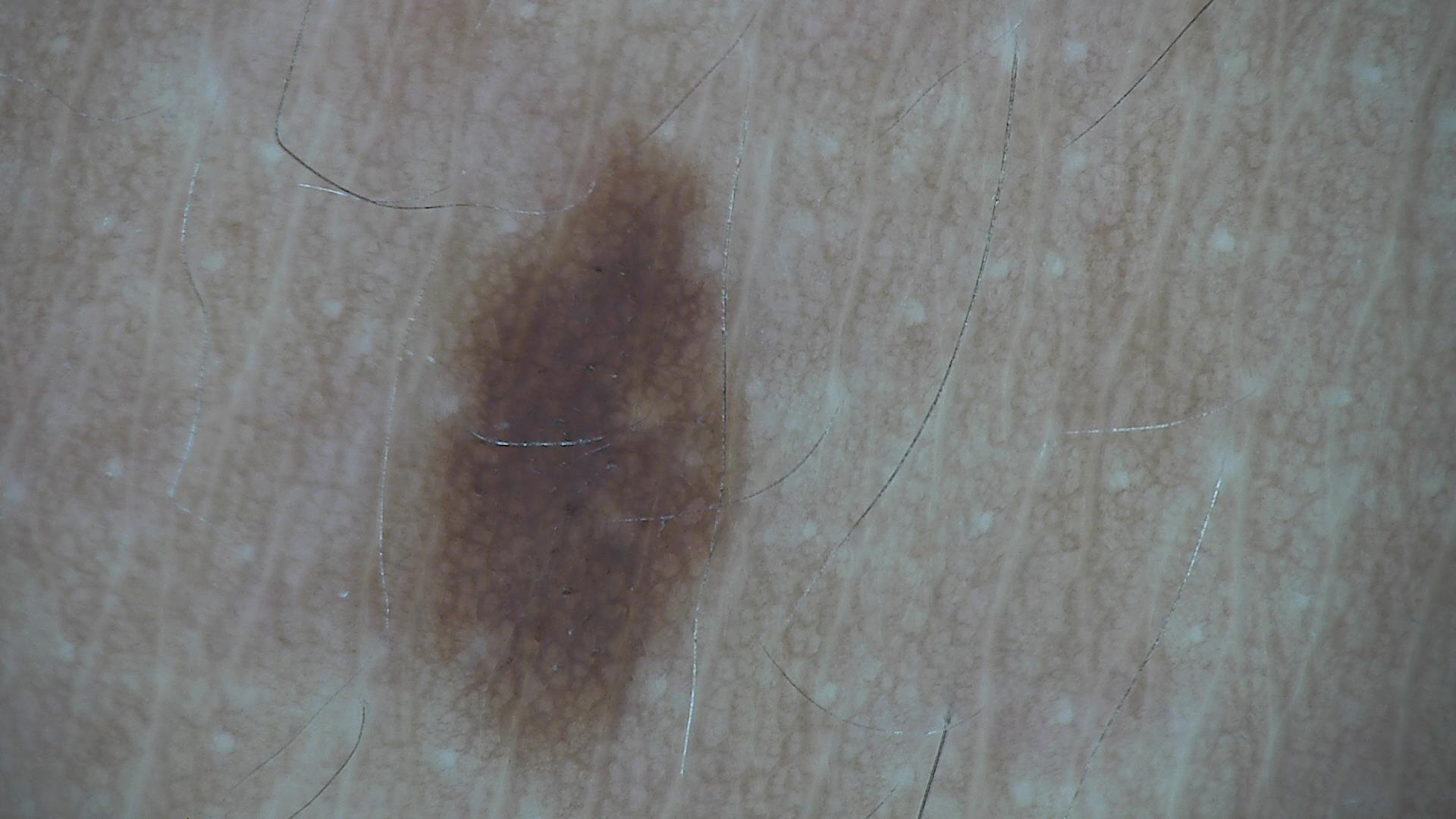{
  "image": "dermatoscopy",
  "diagnosis": {
    "name": "dysplastic junctional nevus",
    "code": "jd",
    "malignancy": "benign",
    "super_class": "melanocytic",
    "confirmation": "expert consensus"
  }
}